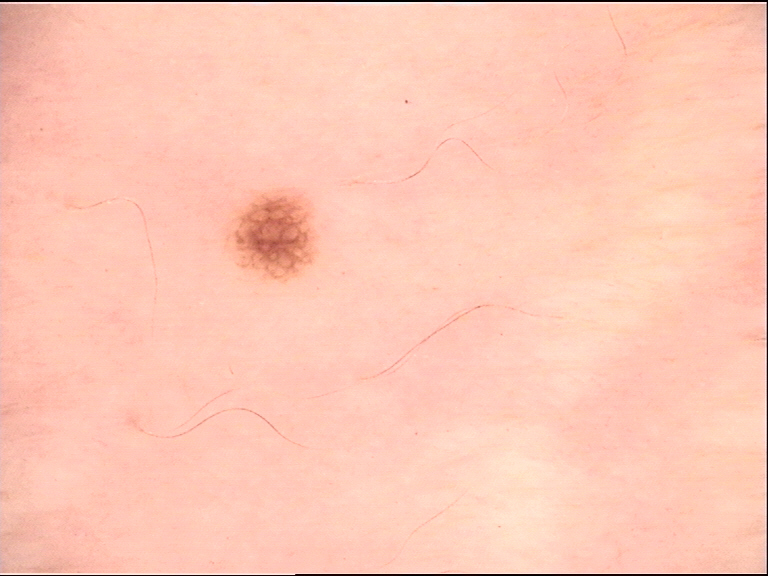{"diagnosis": {"name": "dysplastic junctional nevus", "code": "jd", "malignancy": "benign", "super_class": "melanocytic", "confirmation": "expert consensus"}}